Fitzpatrick III. This image was taken at a distance.
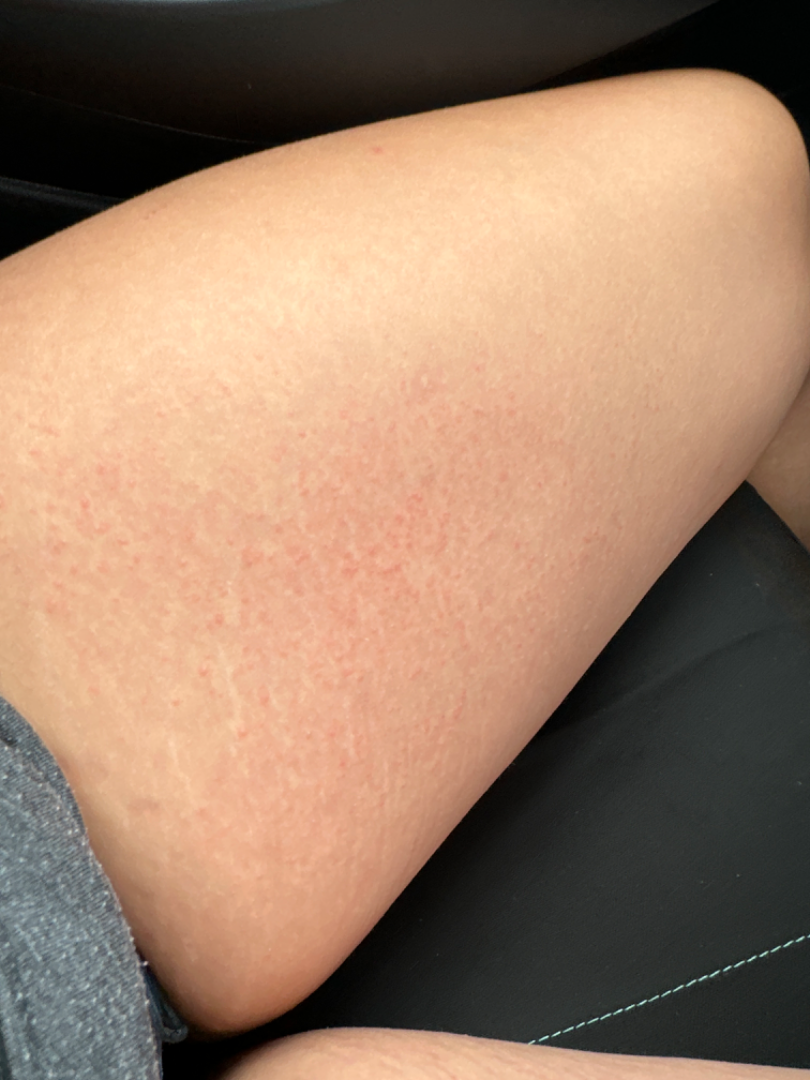assessment: not assessable